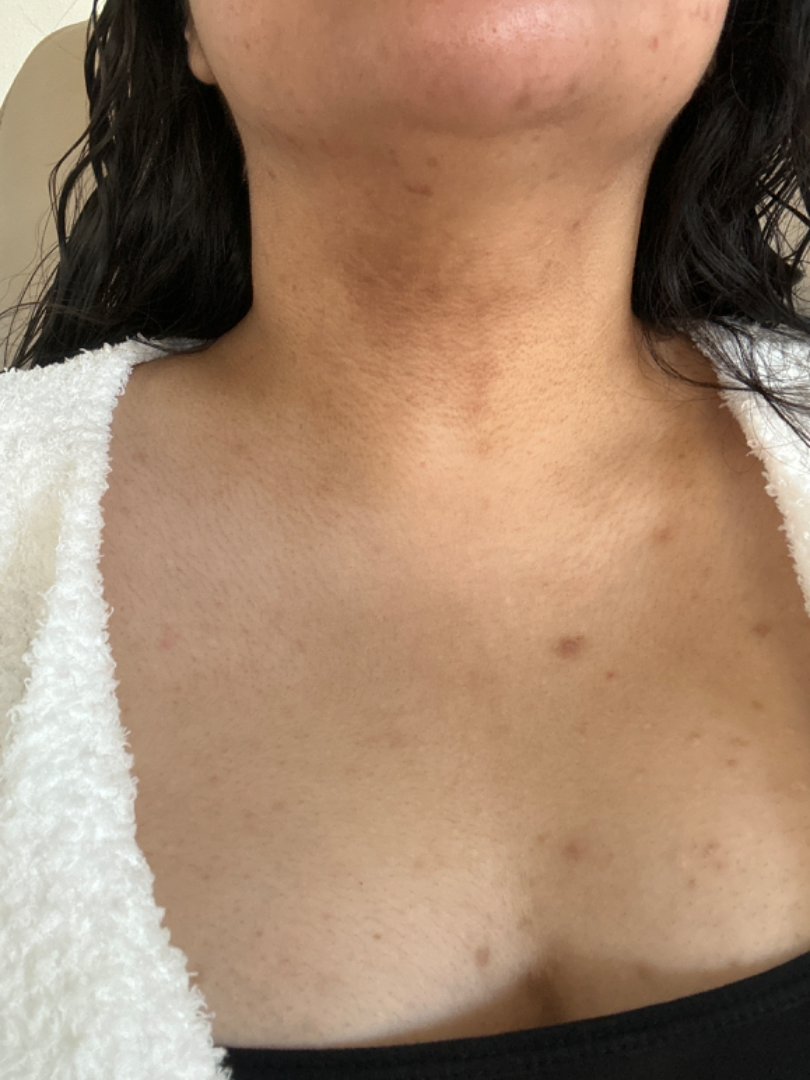On photographic review by a dermatologist: Erythema dyschromicum perstans (0.67); Post-Inflammatory hyperpigmentation (0.33).